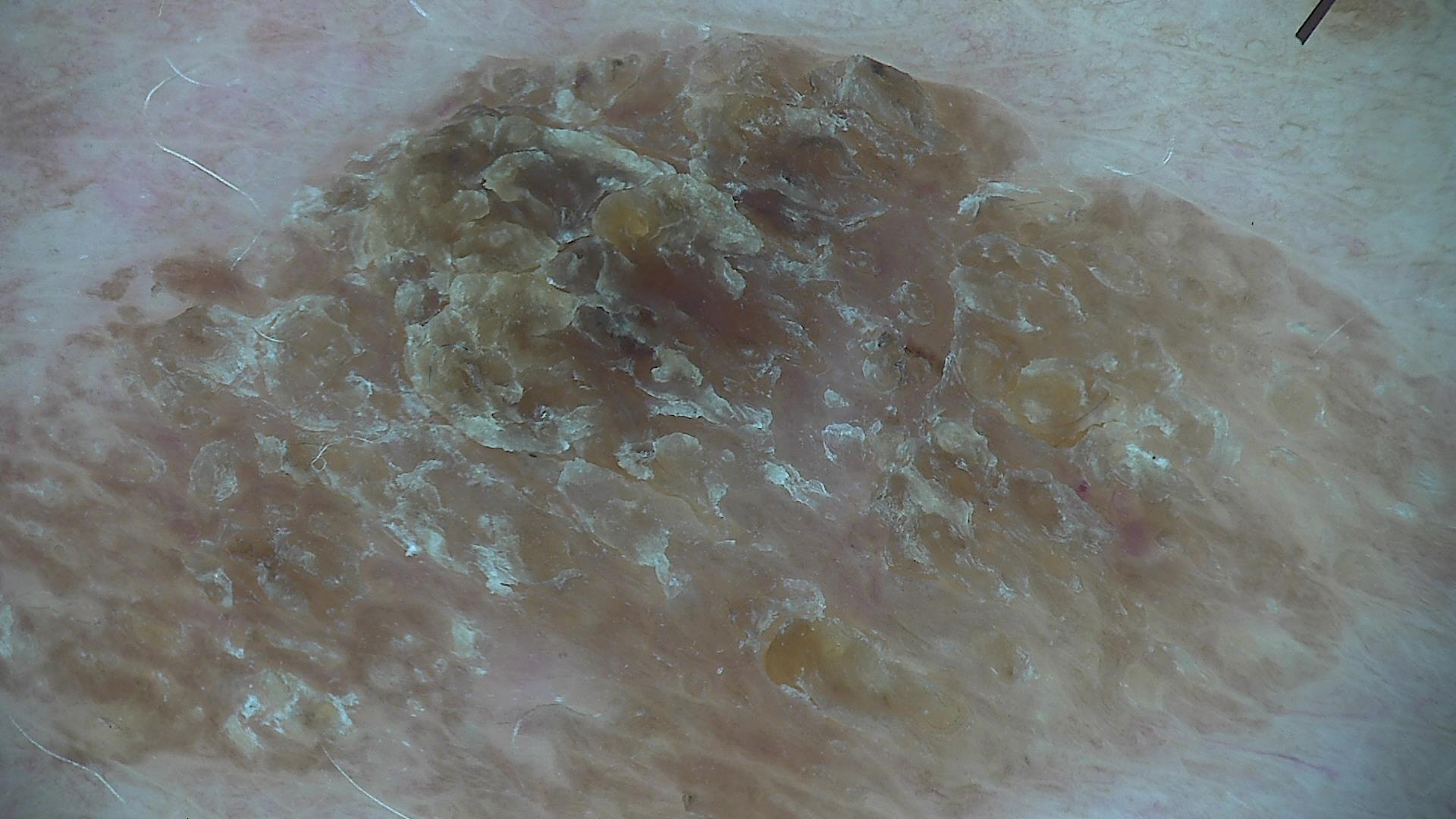A skin lesion imaged with a dermatoscope. The morphology is that of a keratinocytic lesion. Classified as a seborrheic keratosis.